A subject 35 years old; a smartphone photograph of a skin lesion — 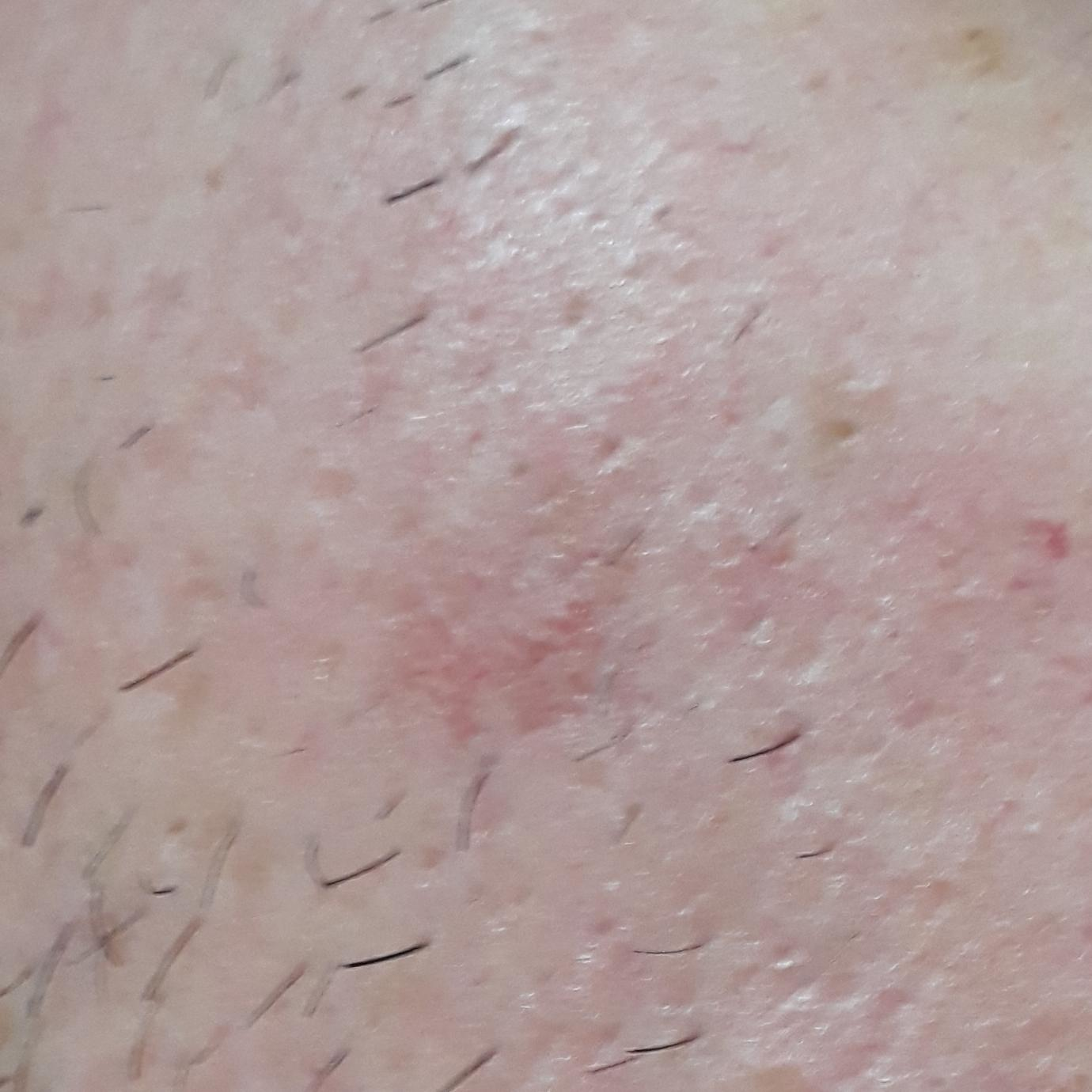site = the face
impression = actinic keratosis (clinical consensus)